The photograph was taken at an angle · located on the arm, back of the hand, leg and front of the torso: 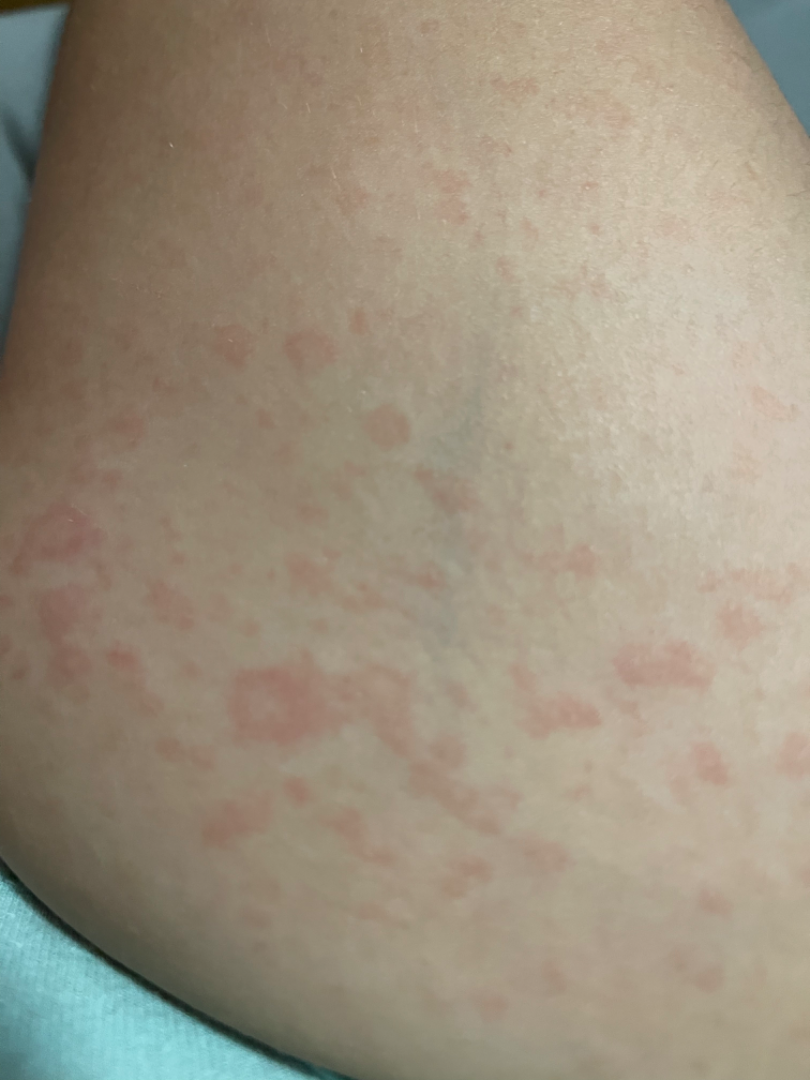The impression was split between Drug Rash and Viral Exanthem.